This is a close-up image. Fitzpatrick II; lay reviewers estimated Monk skin tone scale 2–3 — 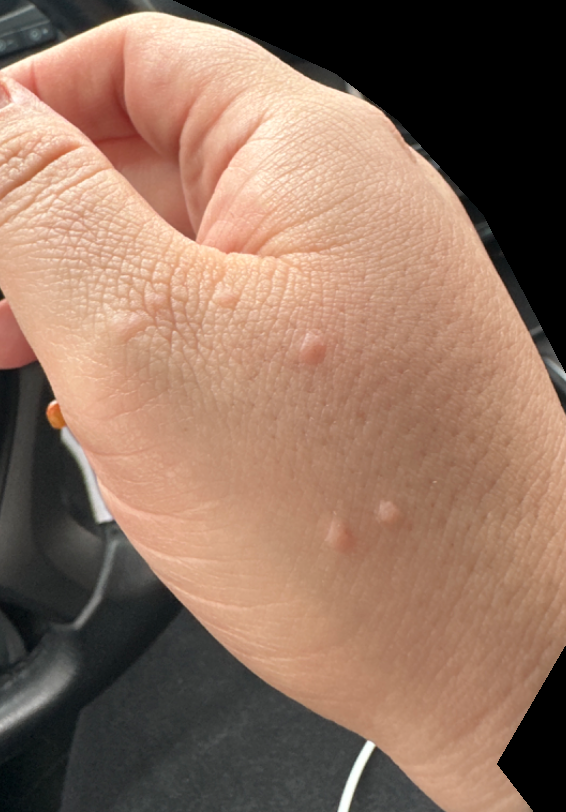• assessment · indeterminate